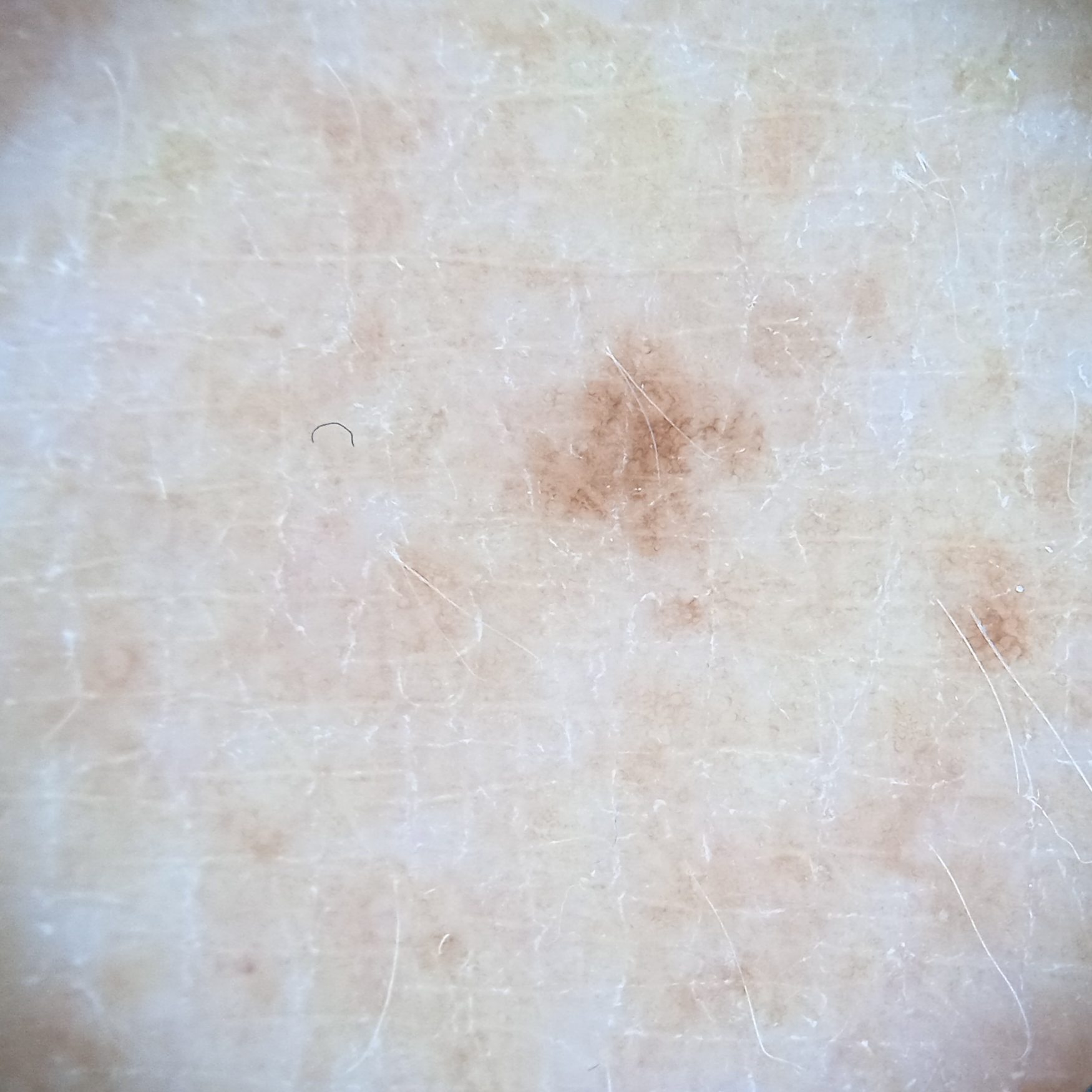<skin_lesion>
  <patient>
    <age>54</age>
    <sex>male</sex>
  </patient>
  <referral>research study (no referral diagnosis)</referral>
  <image>dermoscopic image</image>
  <lesion_location>an arm</lesion_location>
  <lesion_size>
    <diameter_mm>2.6</diameter_mm>
  </lesion_size>
  <diagnosis>
    <name>melanocytic nevus</name>
    <malignancy>benign</malignancy>
  </diagnosis>
</skin_lesion>